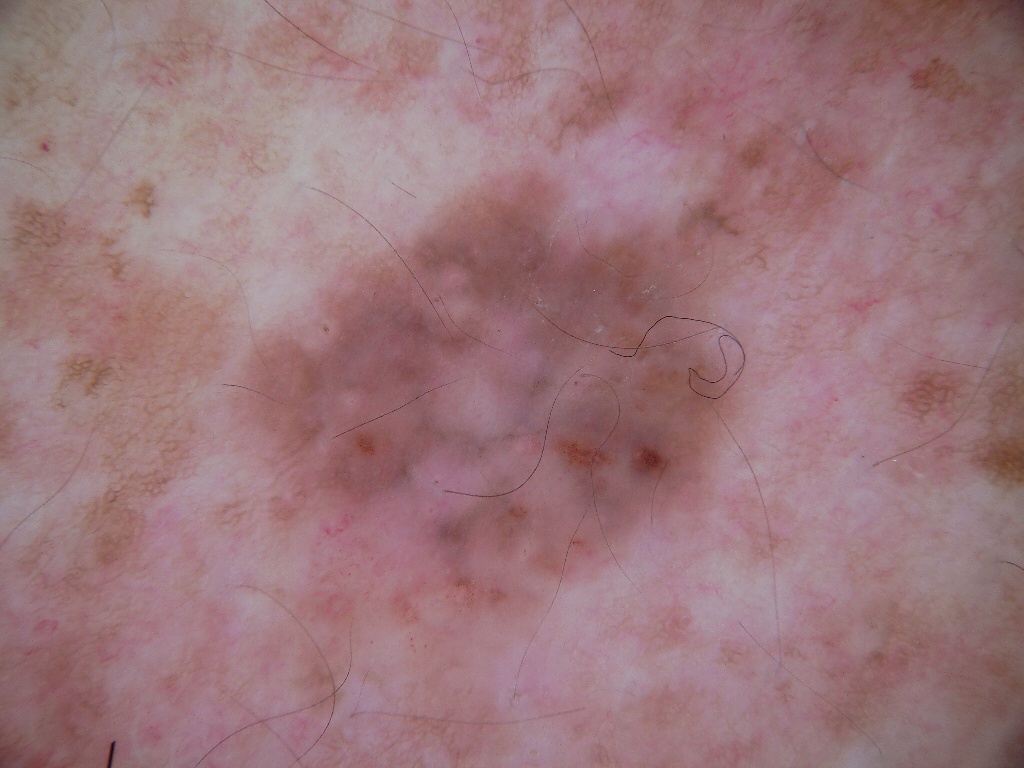<lesion>
  <image>
    <modality>dermoscopy</modality>
  </image>
  <lesion_location>
    <bbox_xyxy>212, 158, 749, 729</bbox_xyxy>
  </lesion_location>
  <dermoscopic_features>
    <present/>
    <absent>streaks, globules</absent>
  </dermoscopic_features>
  <diagnosis>
    <malignancy>benign</malignancy>
    <provenance>clinical</provenance>
  </diagnosis>
</lesion>